The photo was captured at an angle — 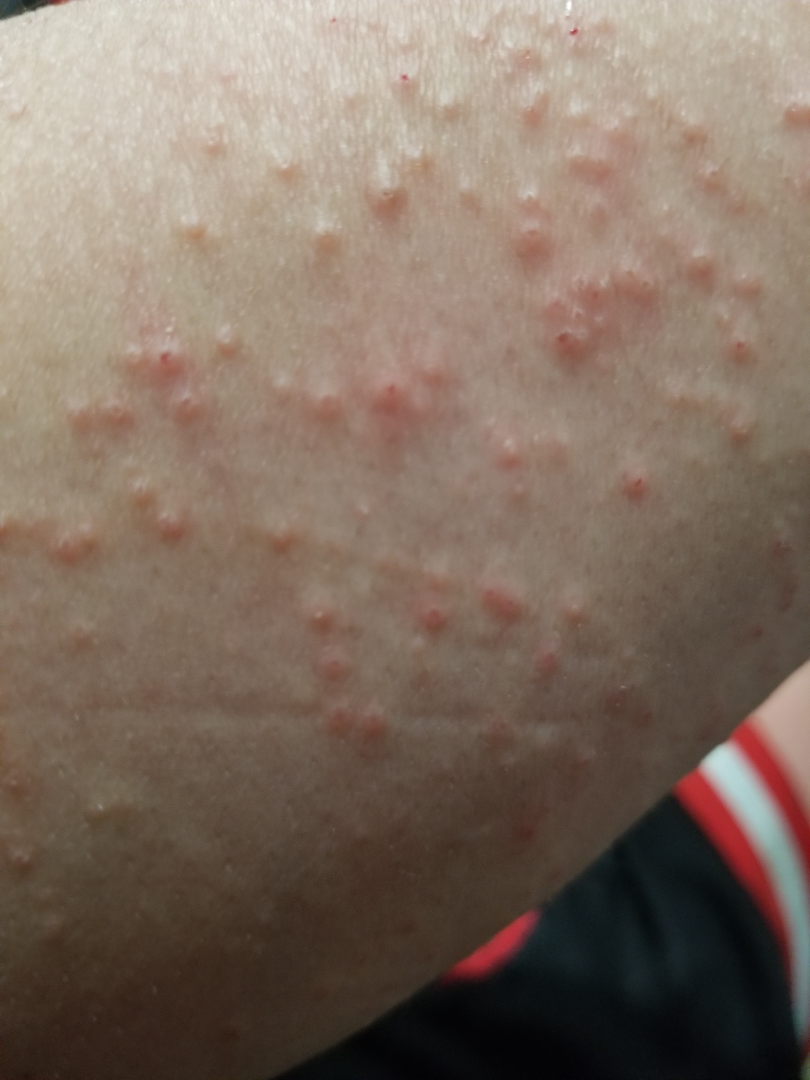<case>
<differential>Allergic Contact Dermatitis</differential>
</case>